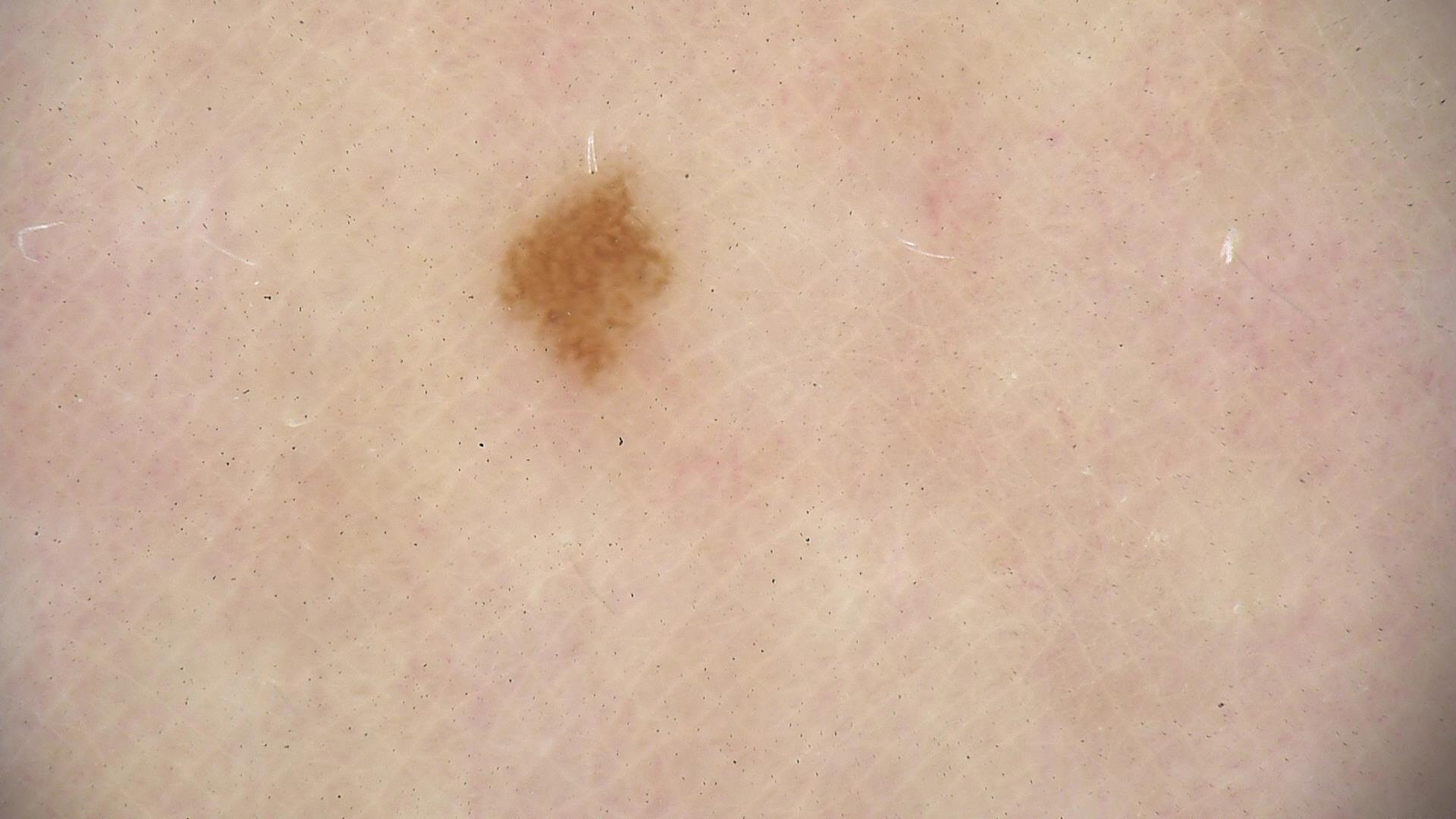  image: dermoscopy
  diagnosis:
    name: junctional nevus
    code: jb
    malignancy: benign
    super_class: melanocytic
    confirmation: expert consensus